A skin lesion imaged with a dermatoscope.
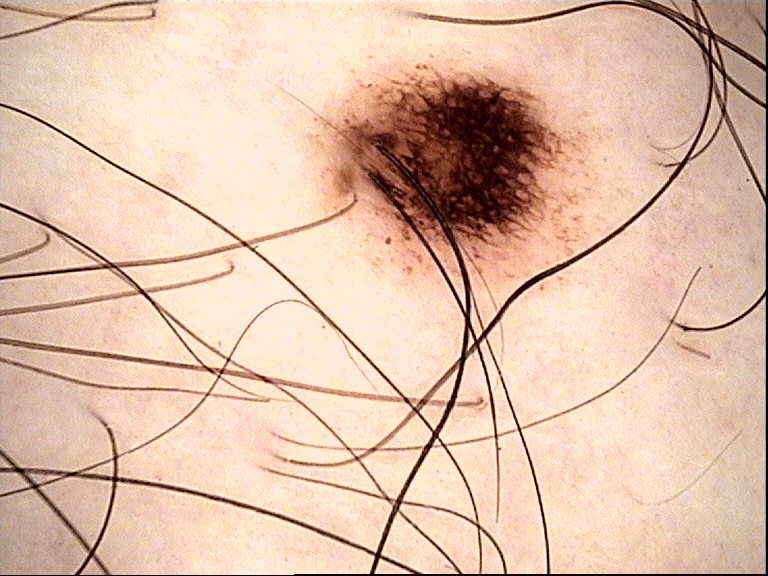Impression:
The diagnosis was a dysplastic junctional nevus.